A clinical photograph of a skin lesion · the patient says their skin tans without first burning · the referring clinician suspected basal cell carcinoma · the patient reports a family history of skin cancer, a personal history of cancer, and no sunbed use · a female patient age 92: 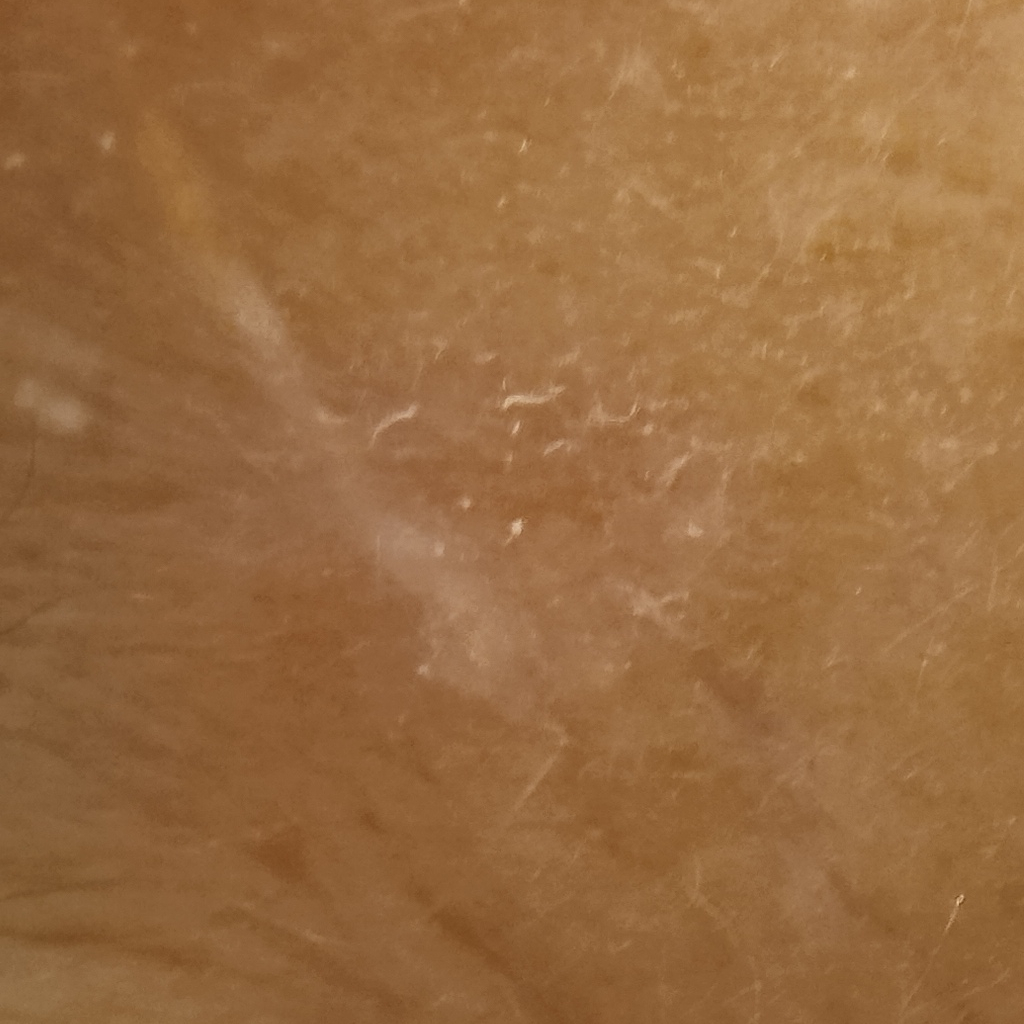lesion_location: the face
lesion_size:
  diameter_mm: 11.5
diagnosis:
  name: basal cell carcinoma
  malignancy: malignant
  procedure: excision
  tumor_thickness_mm: 2.6